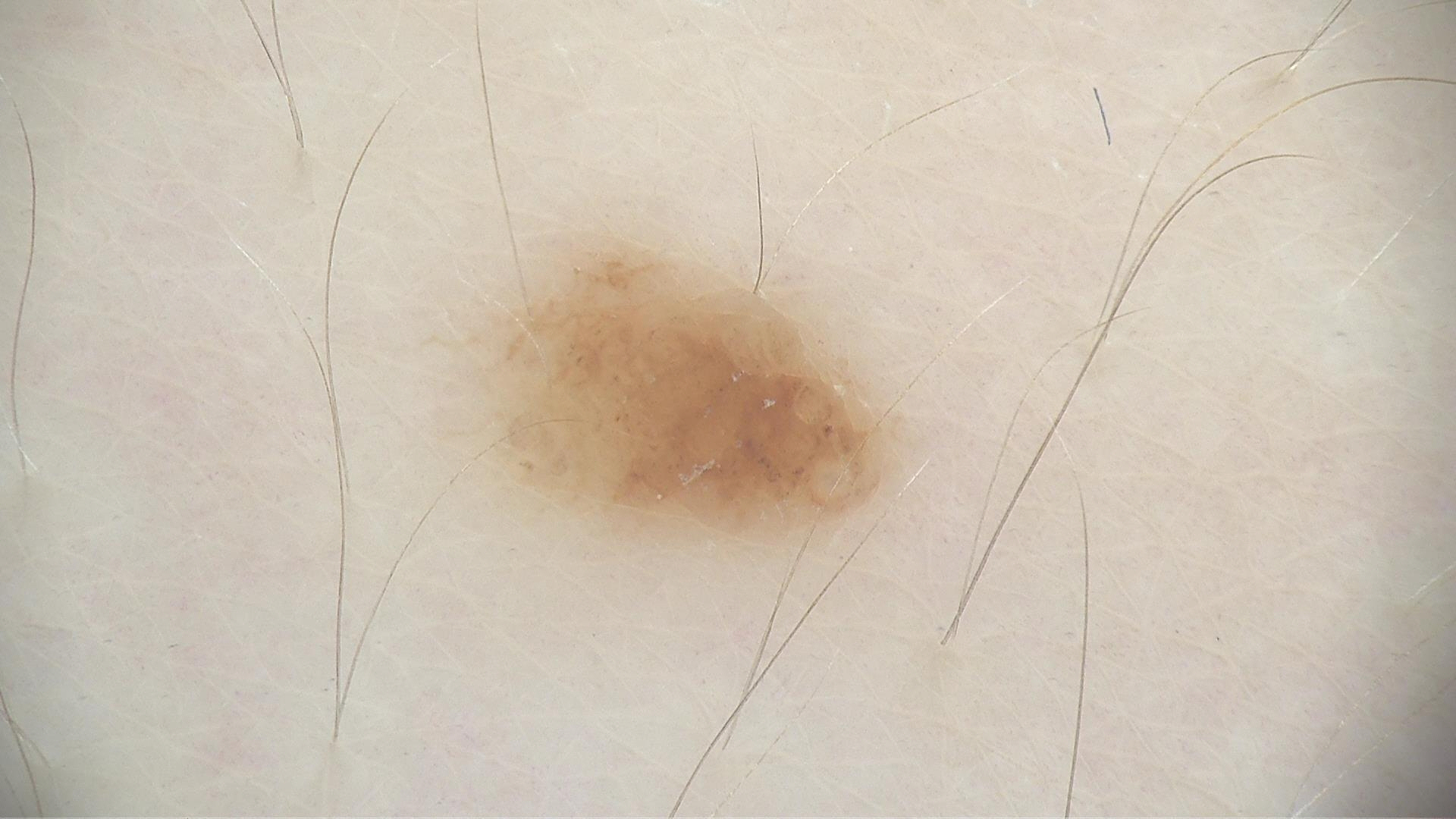Q: What is this lesion?
A: dermal nevus (expert consensus)